The photo was captured at an angle; the subject is female:
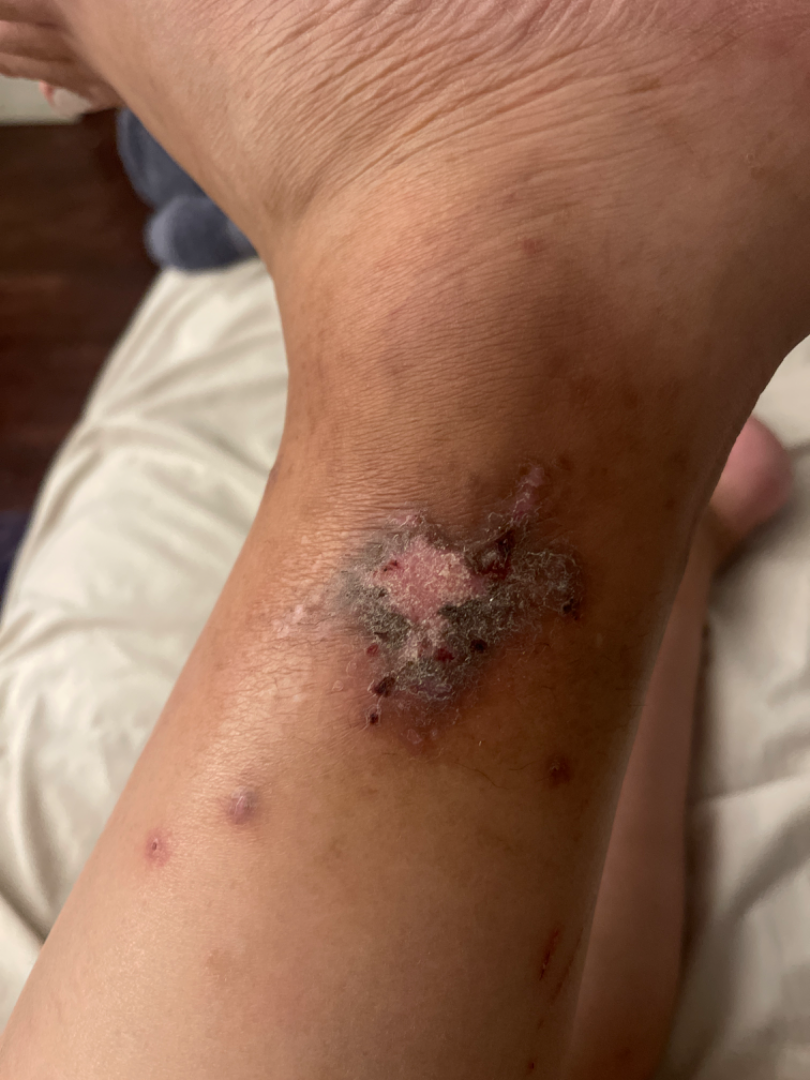  patient_category: a rash
  symptoms:
    - bleeding
    - pain
    - bothersome appearance
    - itching
  systemic_symptoms: fatigue
  duration: since childhood
  texture: rough or flaky
  differential:
    leading:
      - Lichen Simplex Chronicus
    considered:
      - Deep fungal infection
    unlikely:
      - SCC/SCCIS